A dermoscopic photograph of a skin lesion.
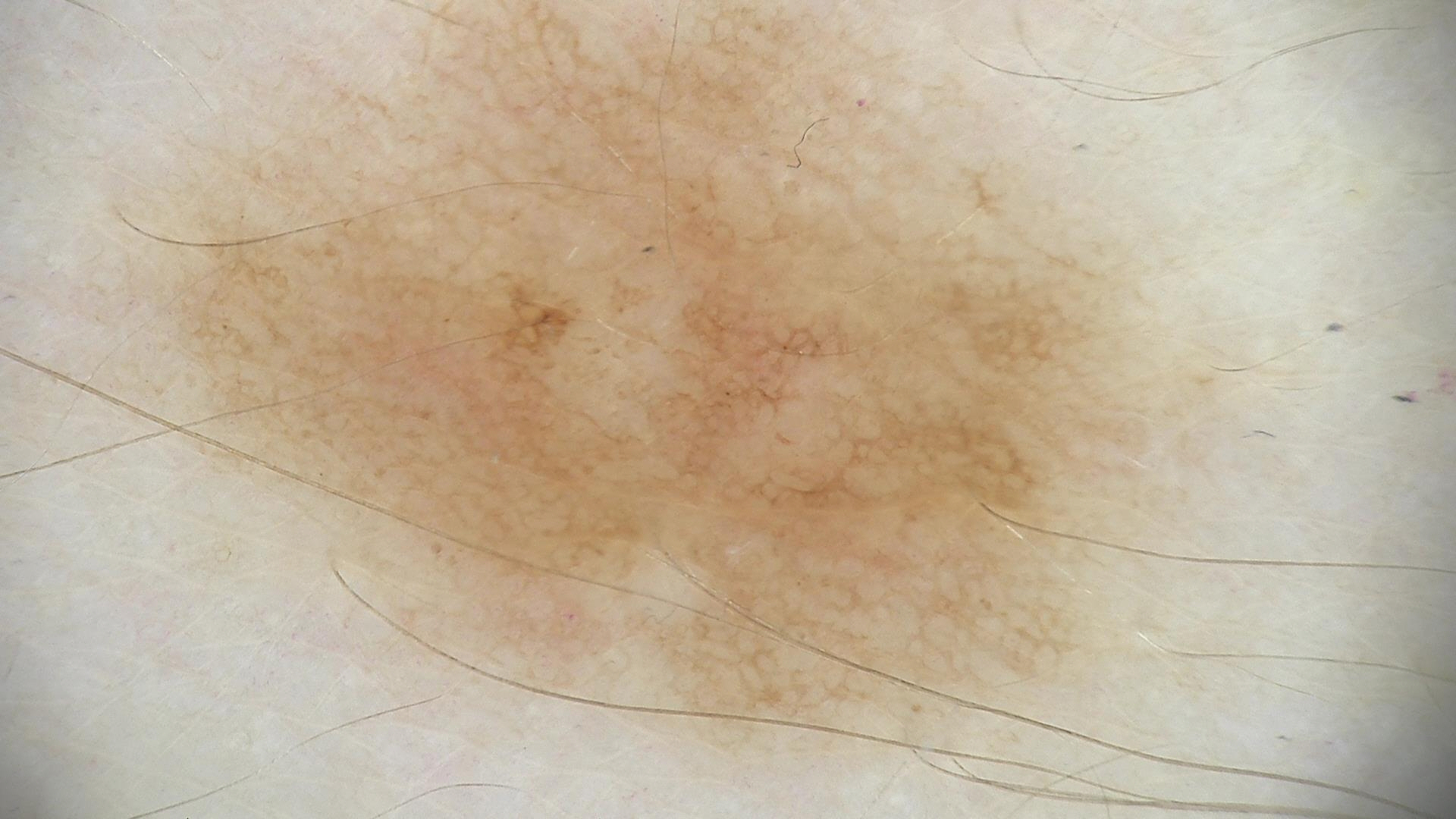Impression:
The diagnostic label was a benign lesion — a dysplastic junctional nevus.